A female patient, aged 43 to 47; a dermoscopic view of a skin lesion — 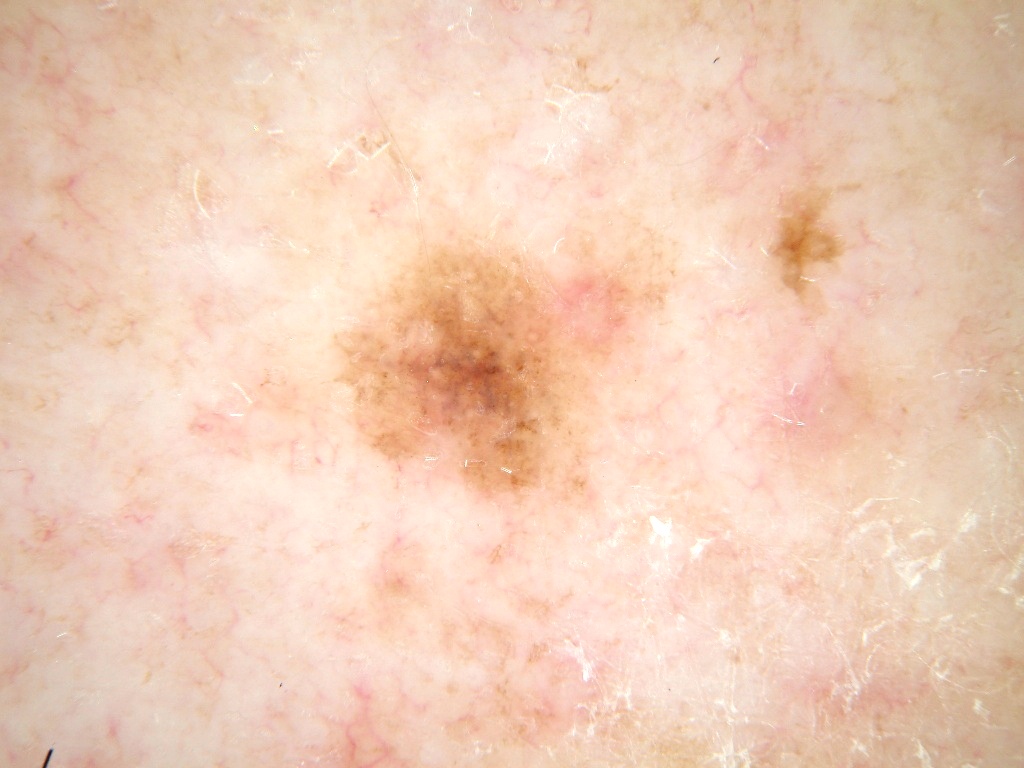The lesion covers approximately 12% of the dermoscopic field.
Dermoscopic assessment notes no milia-like cysts, negative network, globules, streaks, or pigment network.
In (x1, y1, x2, y2) order, the lesion's extent is [298,199,683,511].
Consistent with a melanocytic nevus, a benign lesion.